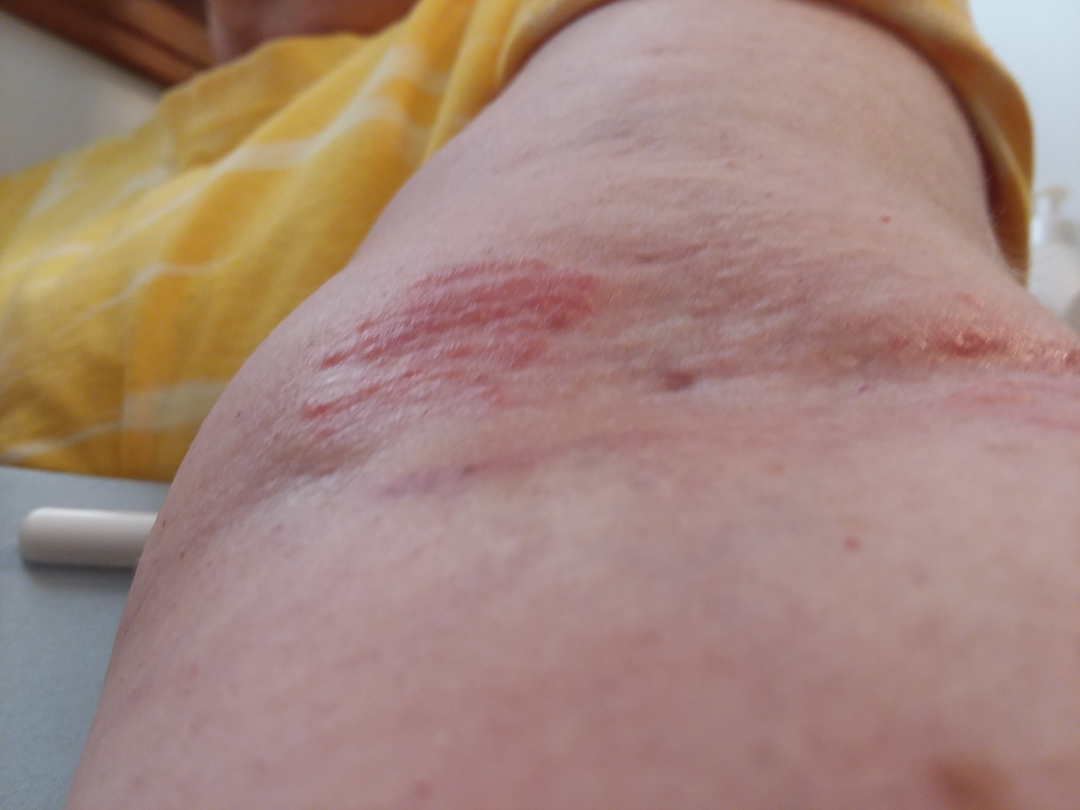Review:
The reviewer was unable to grade this case for skin condition.